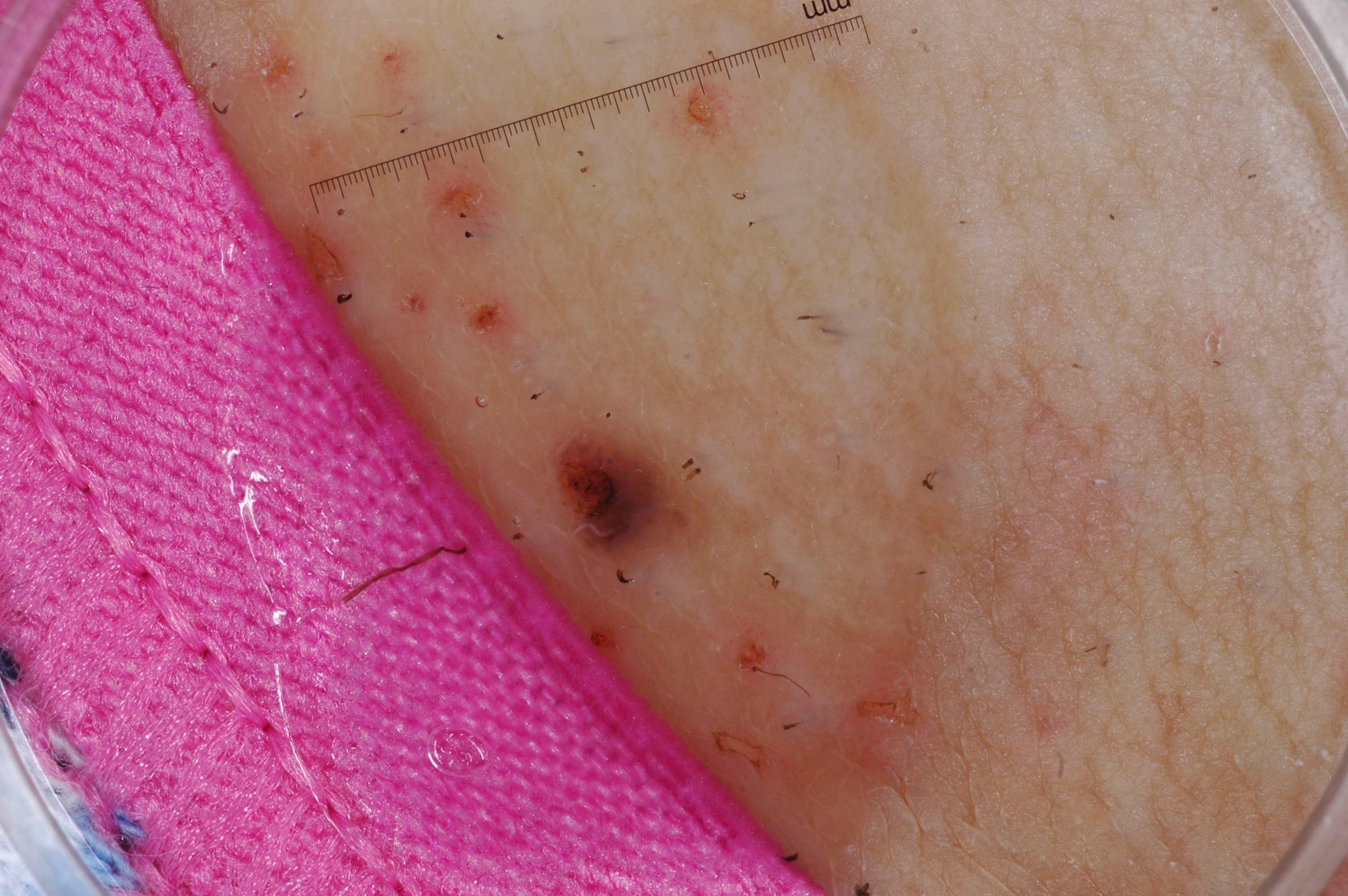– subject · female, aged 23 to 27
– modality · dermoscopy
– extent · small
– dermoscopic features not present · pigment network, negative network, milia-like cysts, and streaks
– lesion bbox · <box>539, 394, 709, 579</box>
– diagnosis · a melanocytic nevus, a benign lesion